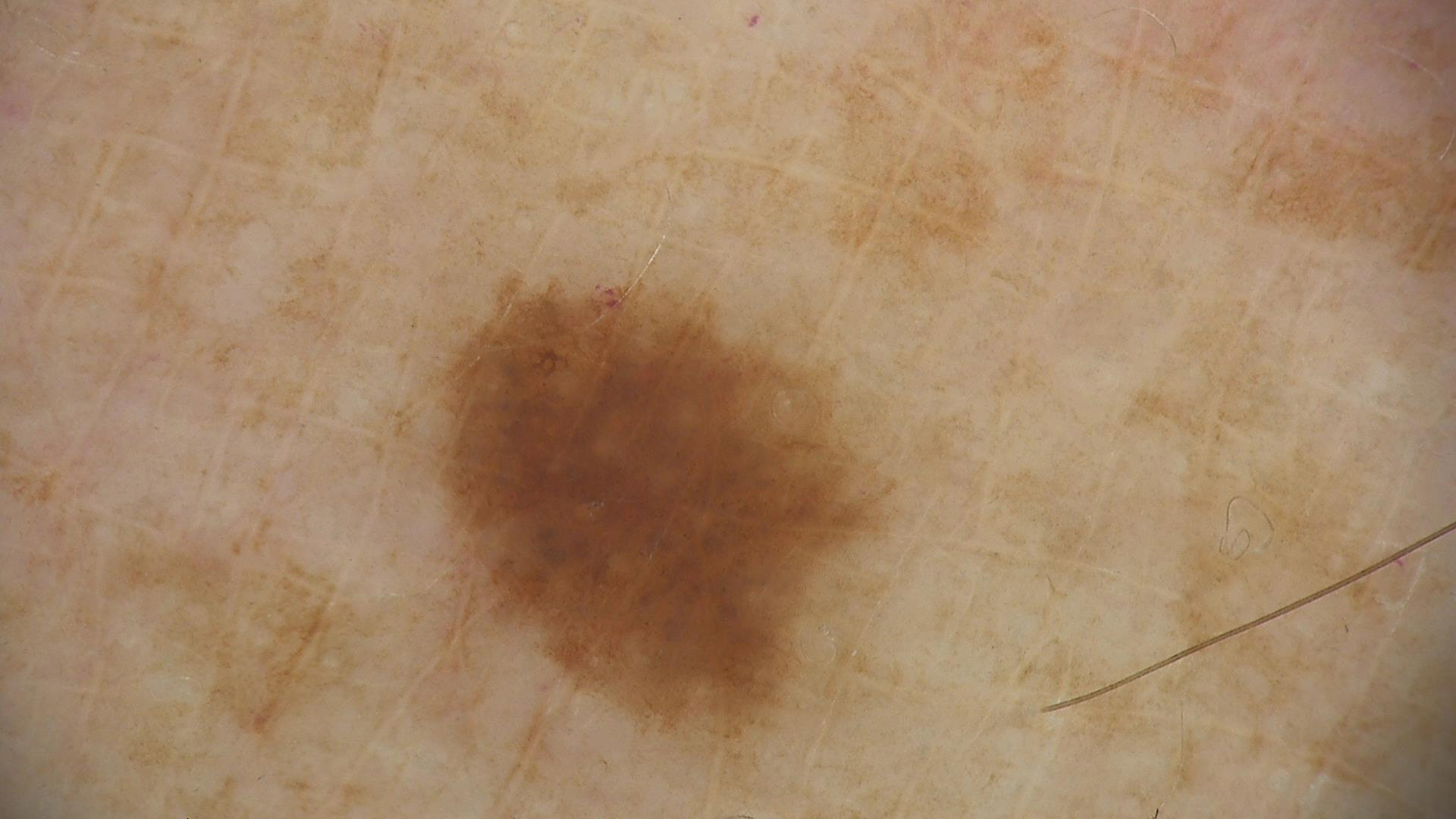Q: What is the imaging modality?
A: dermatoscopy
Q: What was the diagnostic impression?
A: dysplastic junctional nevus (expert consensus)